A dermoscopic close-up of a skin lesion.
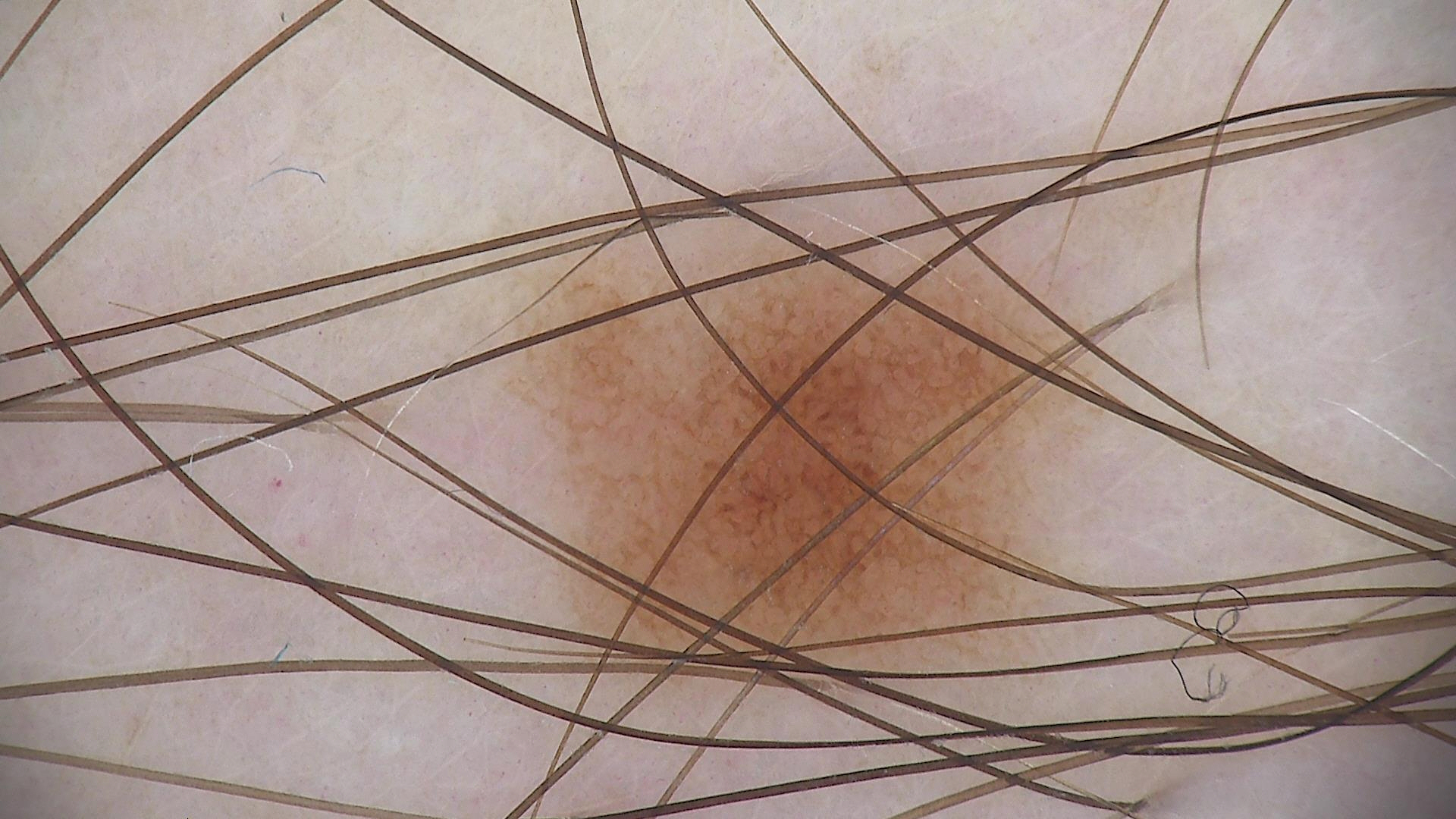<dermoscopy>
<diagnosis>
<name>dysplastic junctional nevus</name>
<code>jd</code>
<malignancy>benign</malignancy>
<super_class>melanocytic</super_class>
<confirmation>expert consensus</confirmation>
</diagnosis>
</dermoscopy>